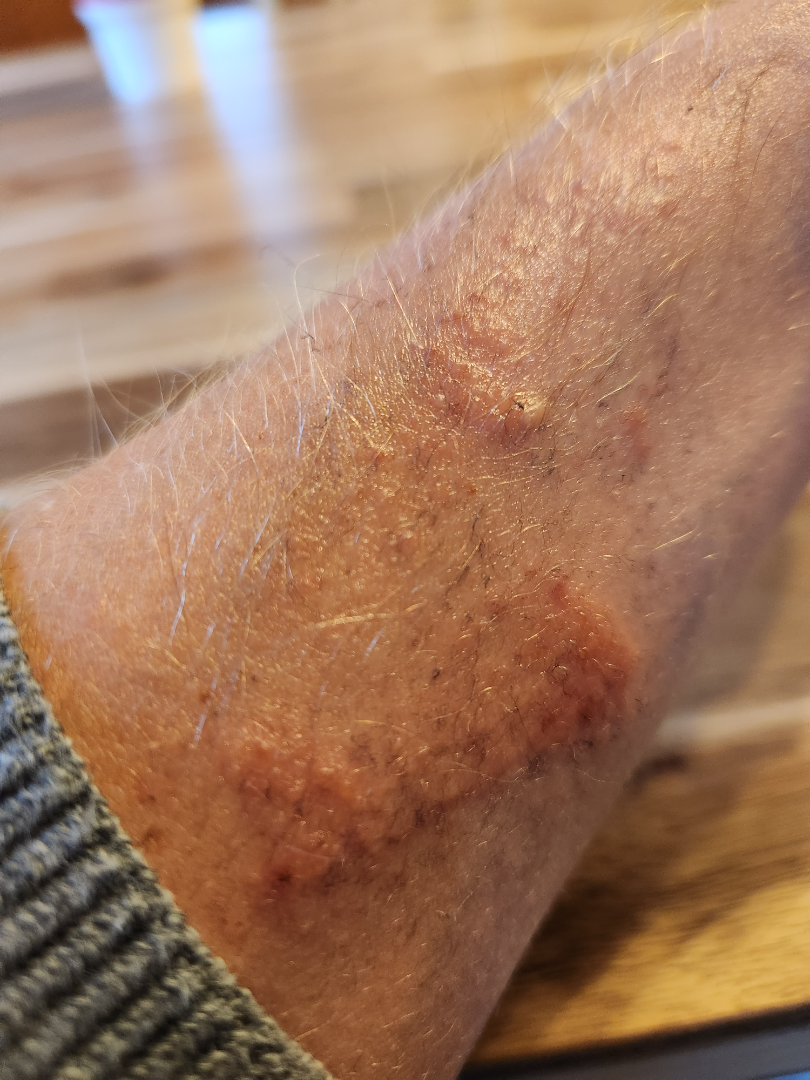  body_site: arm
  duration: less than one week
  texture: raised or bumpy
  patient_category: a rash
  shot_type: close-up
  symptoms:
    - enlargement
    - itching
  differential:
    leading:
      - Allergic Contact Dermatitis